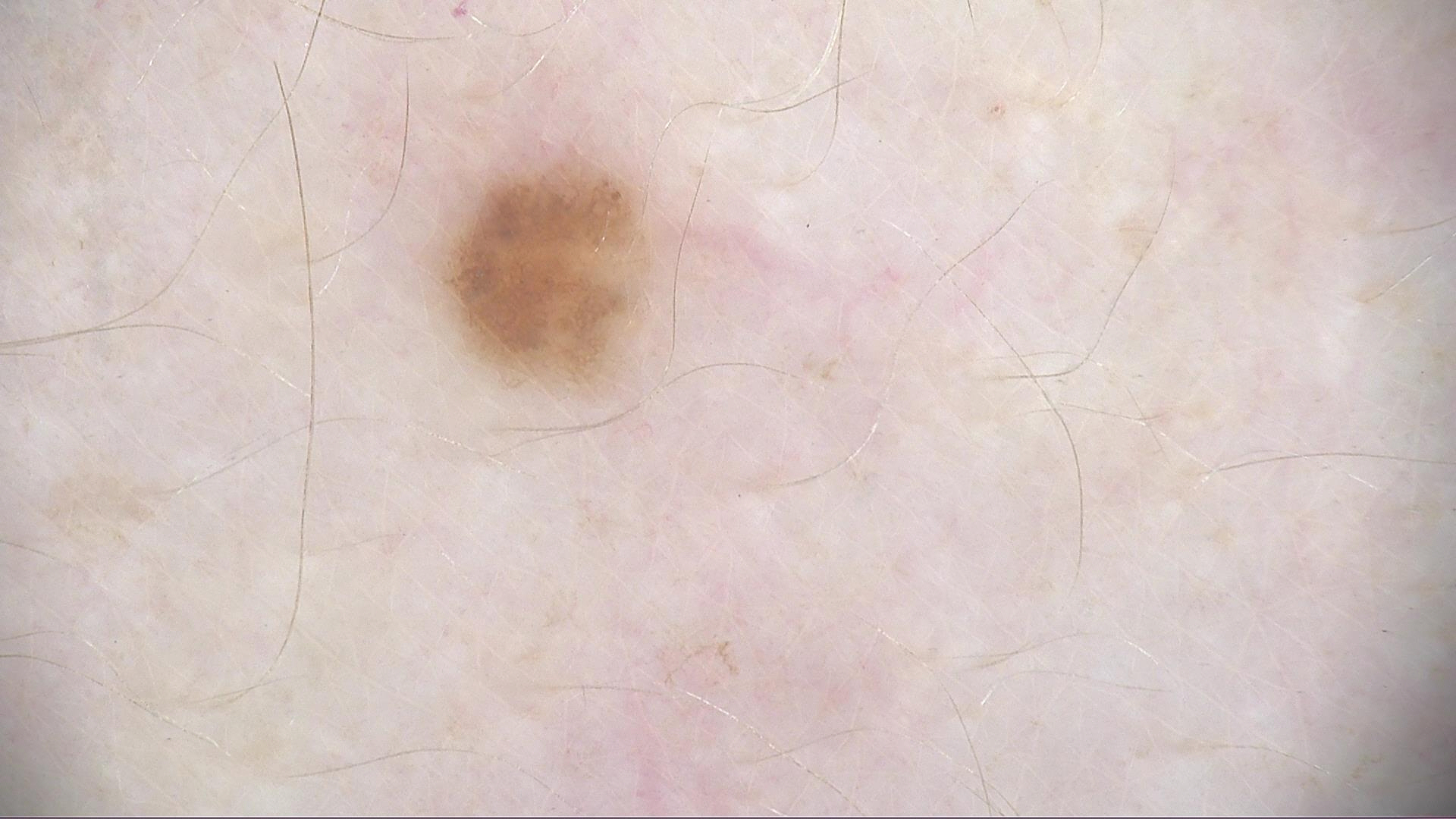Findings:
- label · dysplastic junctional nevus (expert consensus)